The affected area is the arm · the photograph was taken at a distance · the contributor is a female aged 30–39:
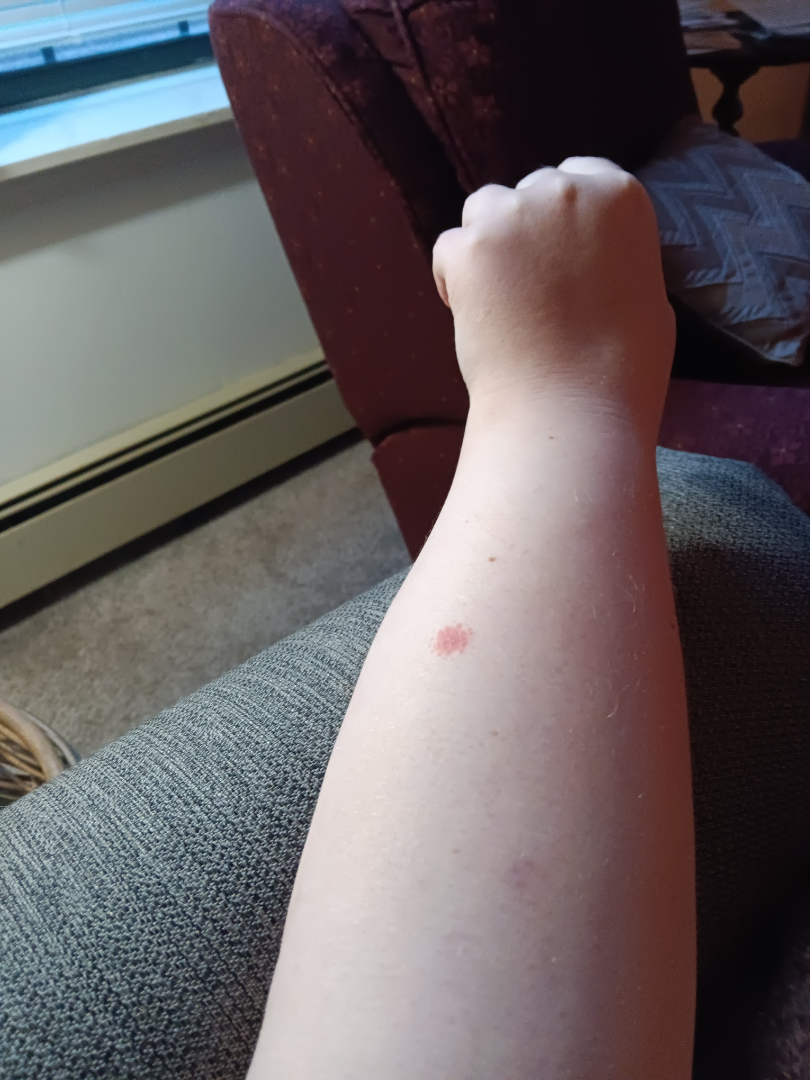Acute dermatitis, NOS and Acute and chronic dermatitis were considered with similar weight.